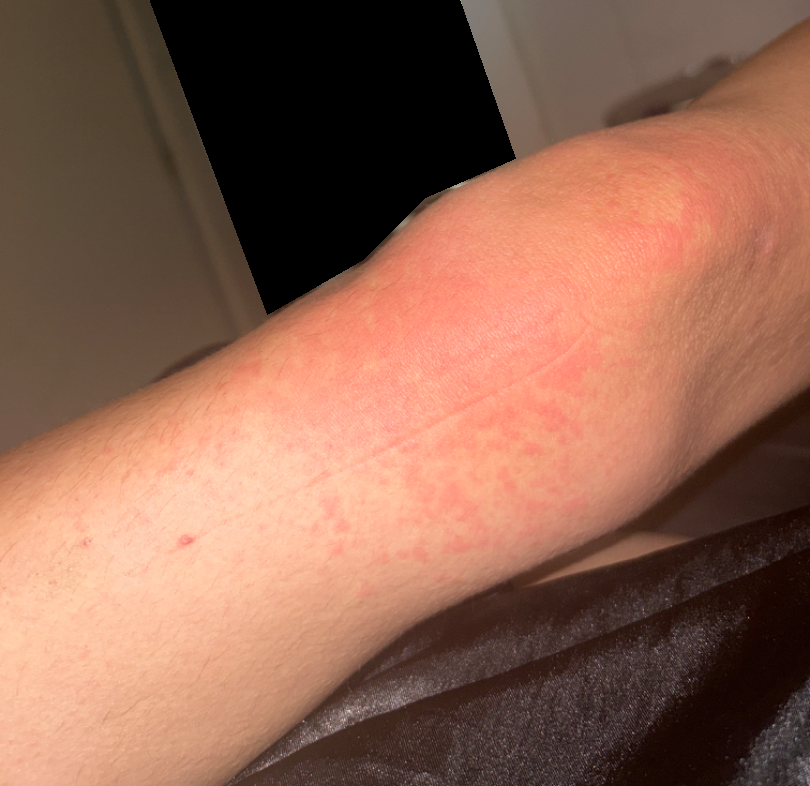{
  "differential": {
    "tied_lead": [
      "Urticaria",
      "Eczema"
    ],
    "unlikely": [
      "Pityriasis rubra pilaris"
    ]
  }
}